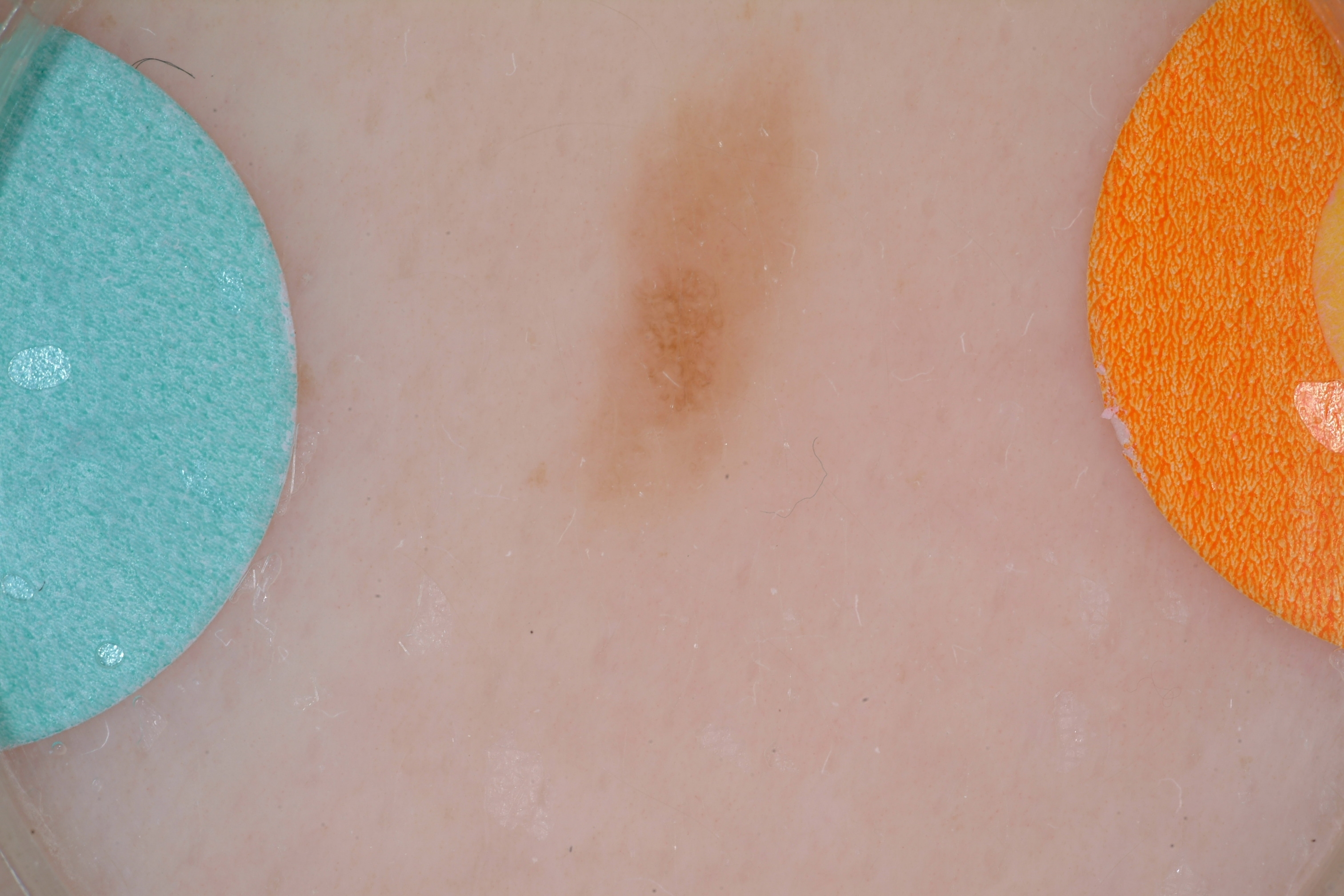modality = dermoscopic image; extent = ~6% of the field; dermoscopic features not present = streaks and globules; location = bbox=[581, 42, 823, 515]; diagnosis = a benign lesion.